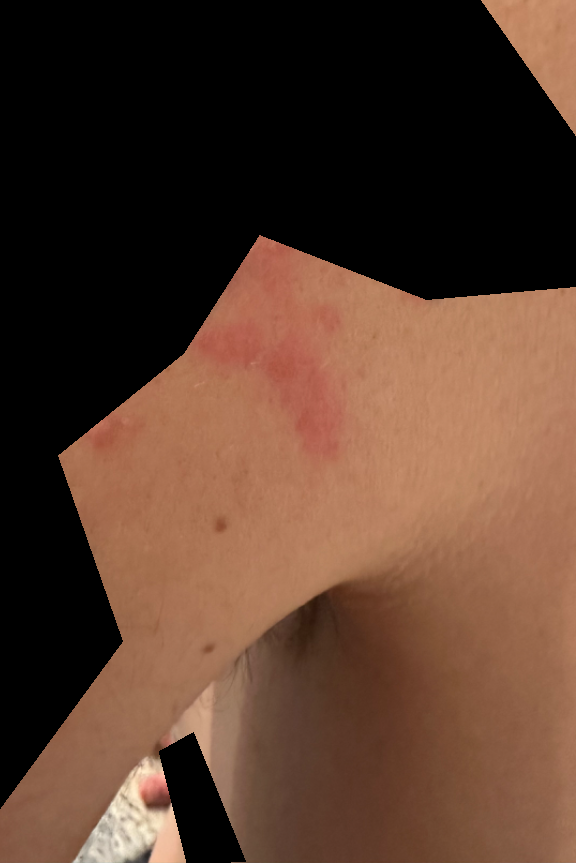Assessment:
The case was indeterminate on photographic review.
Clinical context:
This is a close-up image. The arm is involved.